A skin lesion imaged with a dermatoscope; the patient is a female approximately 65 years of age — 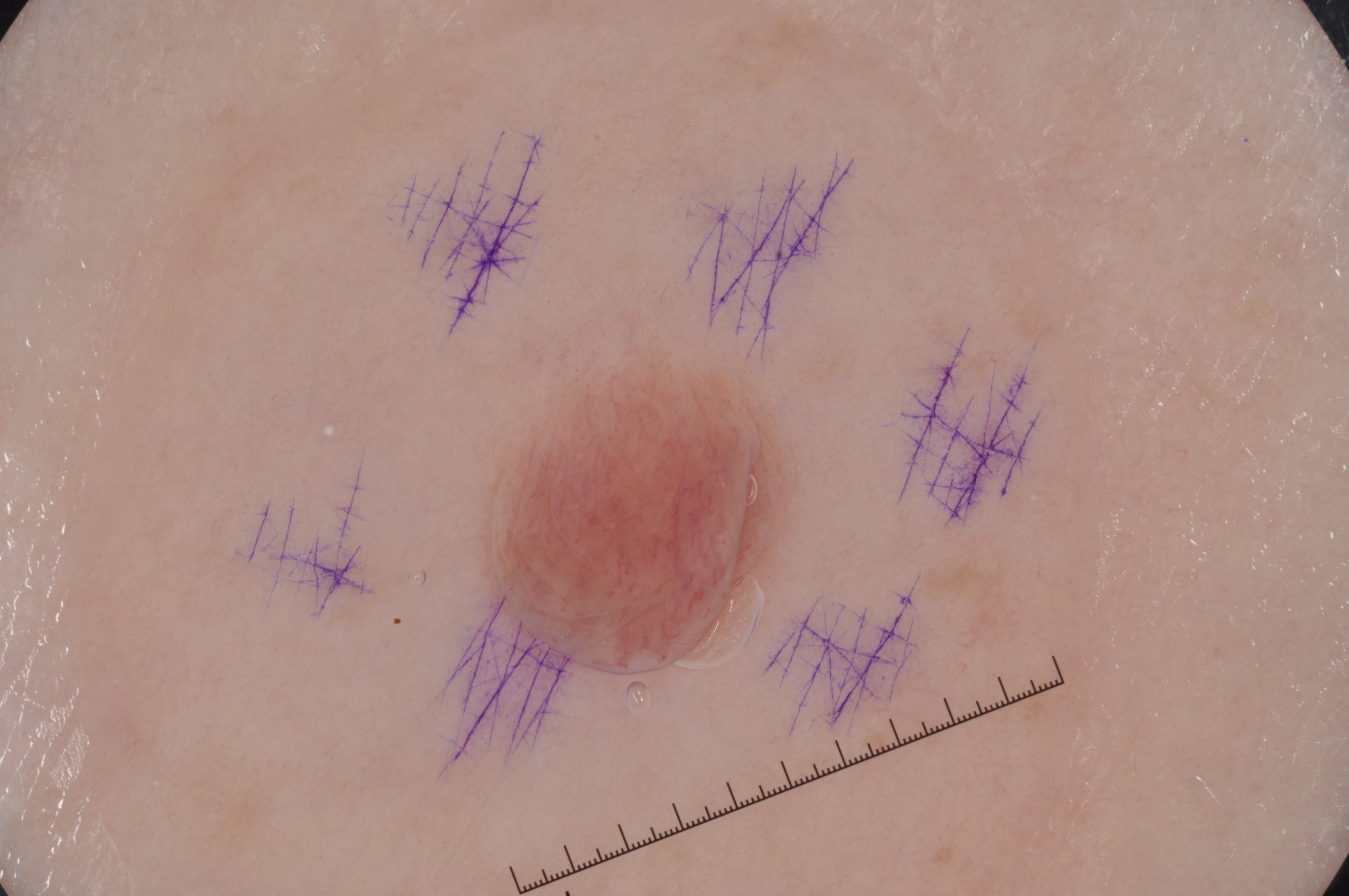lesion location: bbox=[485, 357, 790, 672]
dermoscopic features not present: negative network, pigment network, milia-like cysts, and streaks
diagnostic label: a melanocytic nevus, a benign skin lesion